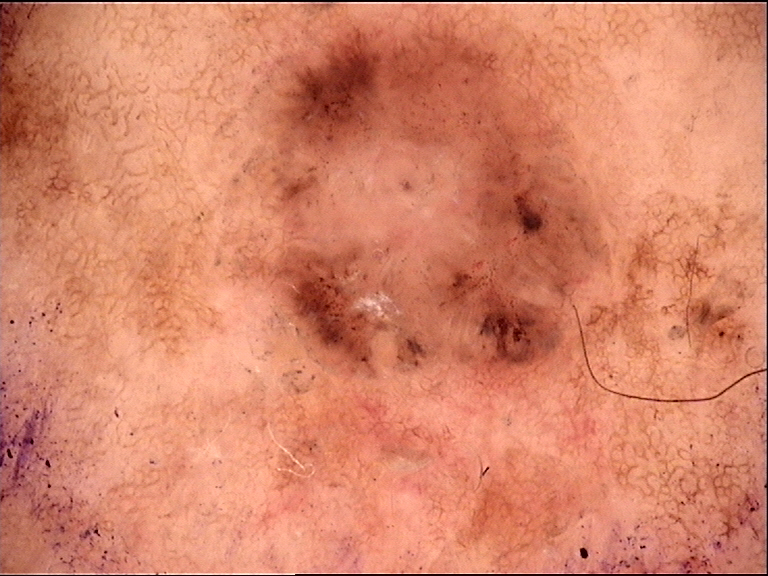image=dermatoscopy | diagnostic label=basal cell carcinoma (biopsy-proven).